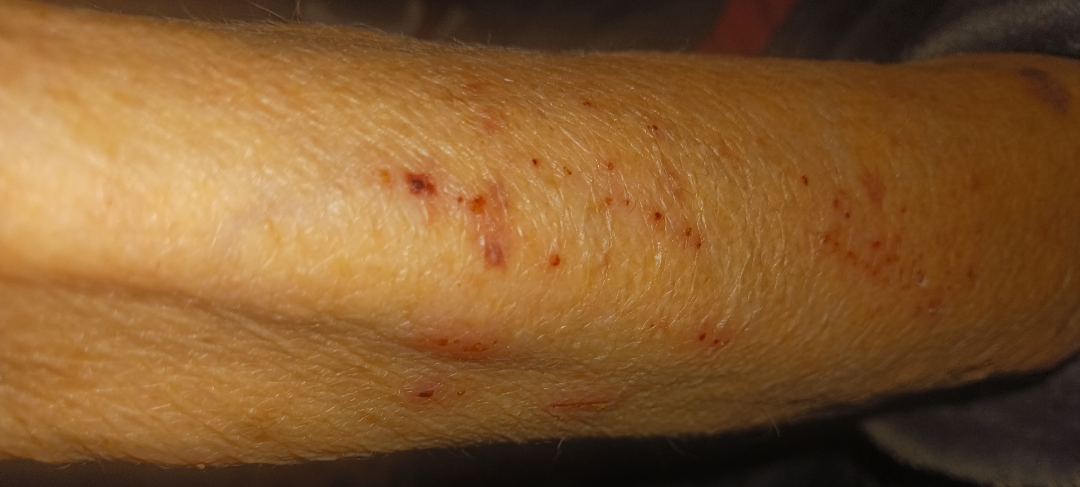described texture: raised or bumpy
framing: at an angle
anatomic site: head or neck, arm and leg